Dermoscopy of a skin lesion:
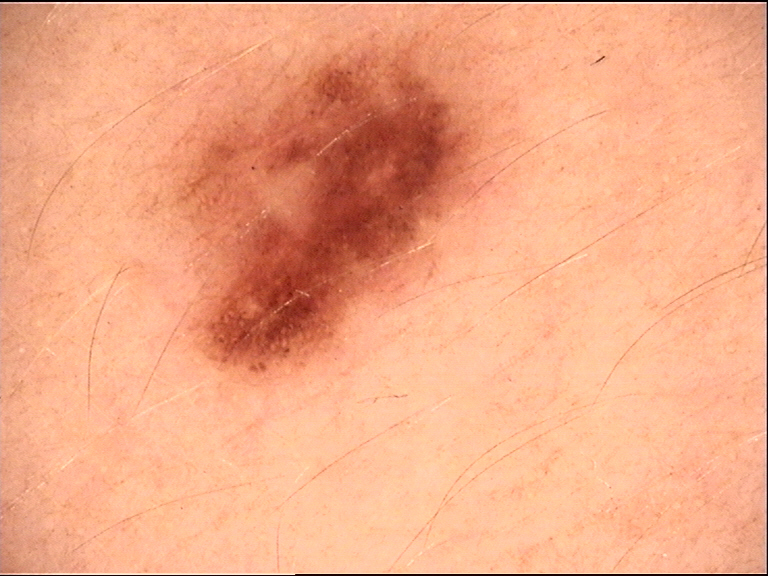The diagnosis was a benign lesion — a dysplastic junctional nevus.